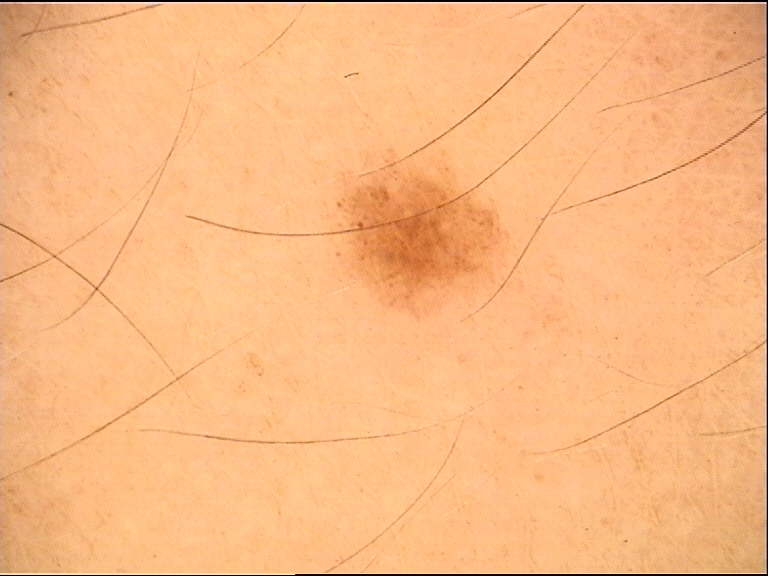Summary: A skin lesion imaged with a dermatoscope. Impression: Consistent with a dysplastic compound nevus.